By history, no prior malignancy (patient or family). A female subject in their 60s. Skin type III. A clinical photo of a skin lesion taken with a smartphone: 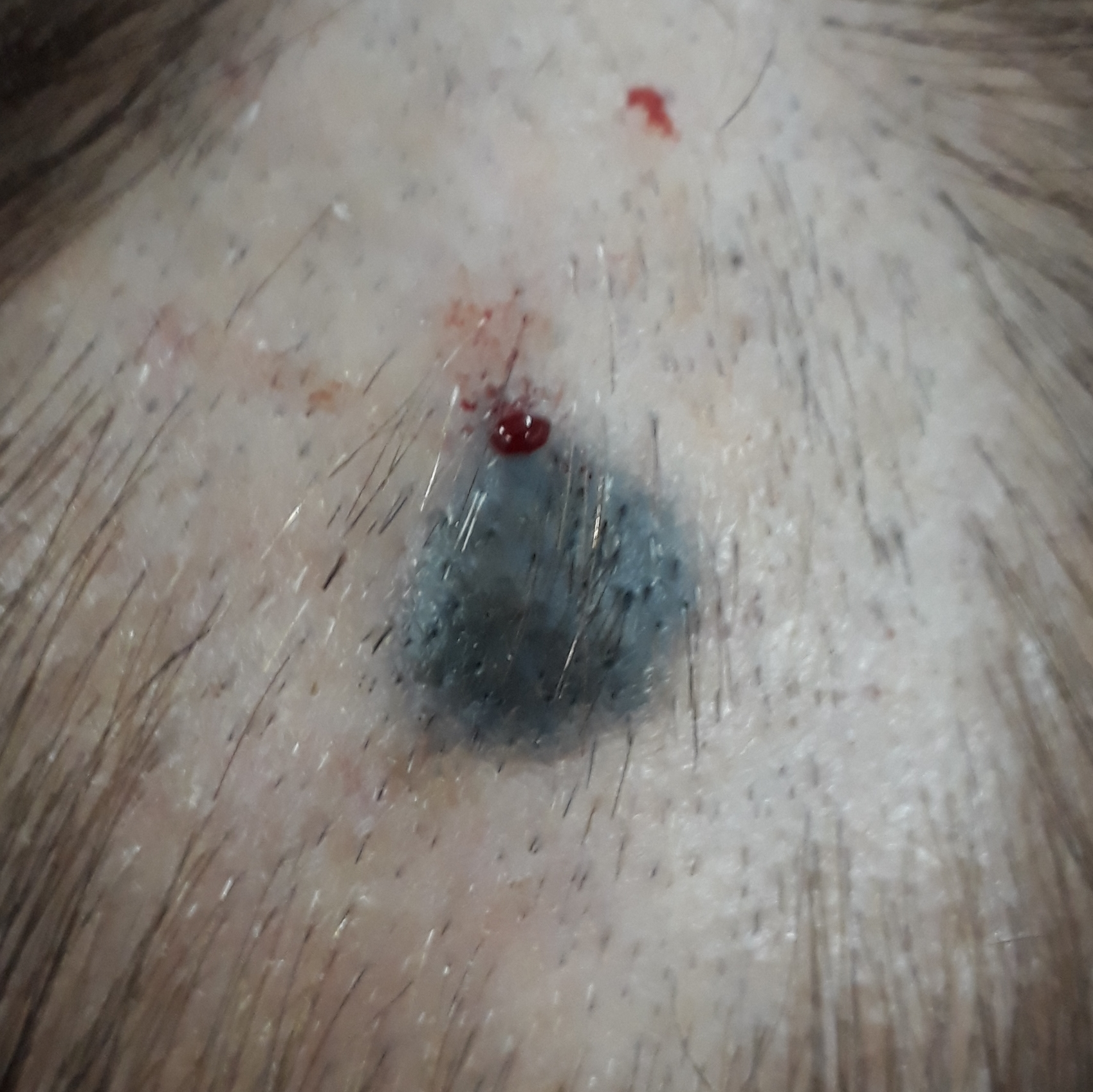| key | value |
|---|---|
| size | 17x15 mm |
| symptoms | itching |
| diagnosis | nevus (biopsy-proven) |